The patient indicates the lesion is raised or bumpy. The patient is 70–79, male. The patient considered this a rash. Reported duration is less than one week. Skin tone: Fitzpatrick III; non-clinician graders estimated a MST of 3. The affected area is the back of the torso. The lesion is associated with burning and itching. Close-up view:
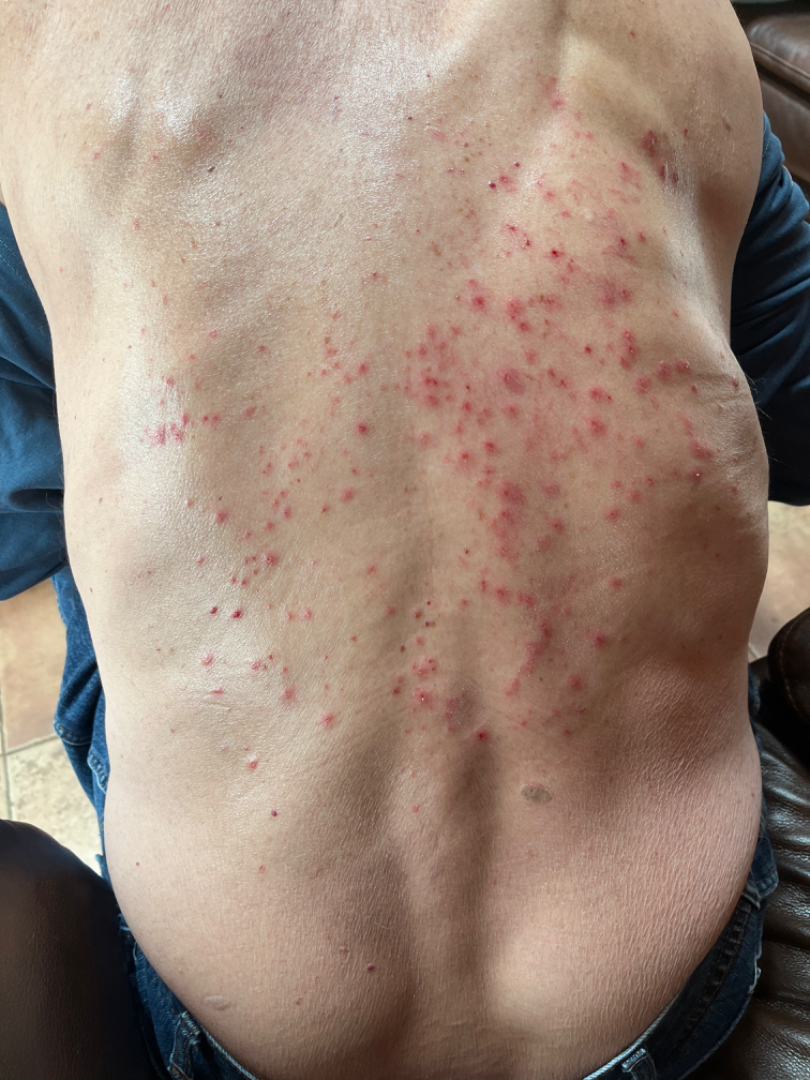{"differential": {"tied_lead": ["Miliaria", "Folliculitis"], "unlikely": ["Grover's disease"]}}